A dermoscopic image of a skin lesion. A female patient aged around 55.
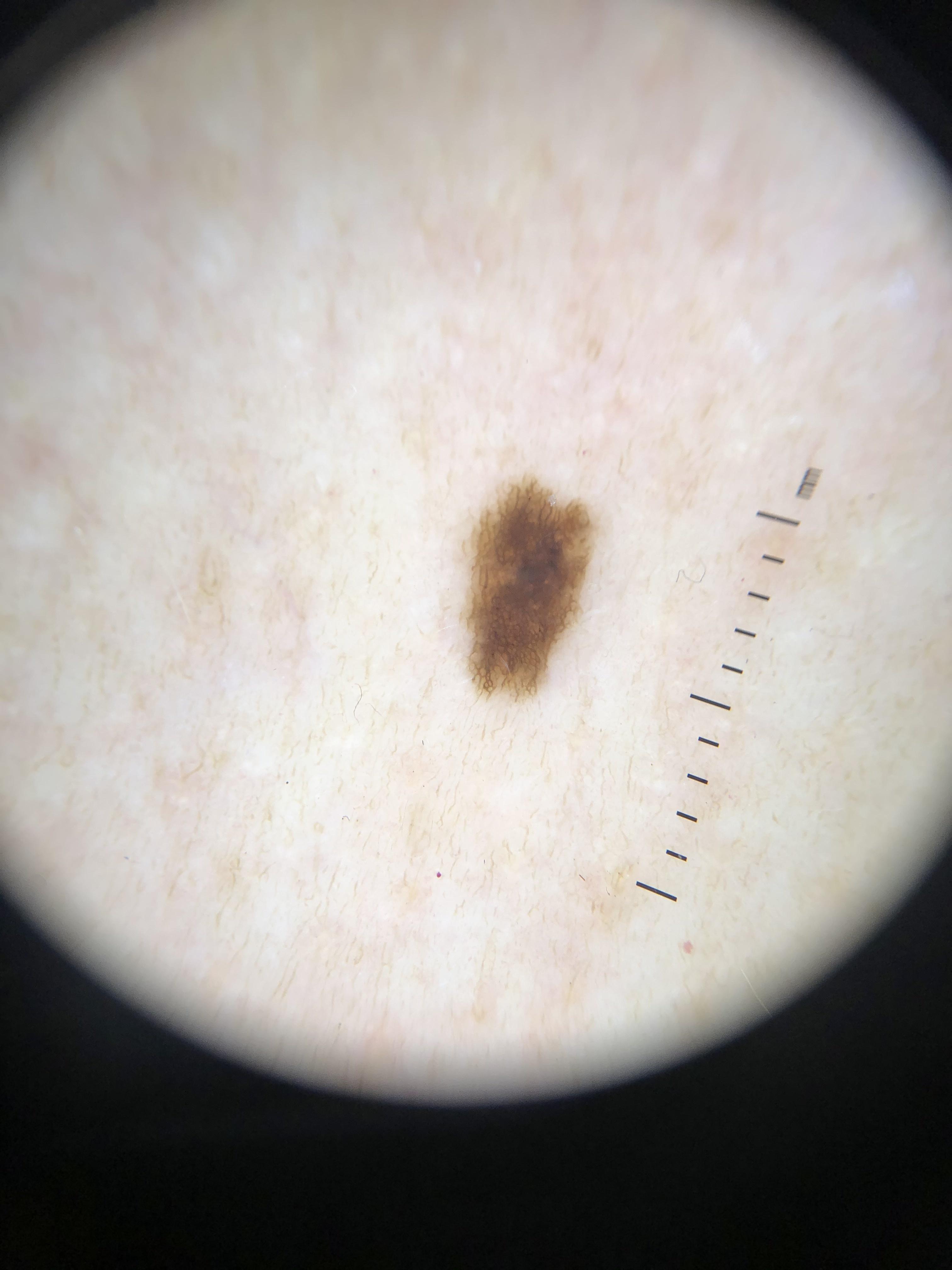Confirmed on histopathology as a nevus.